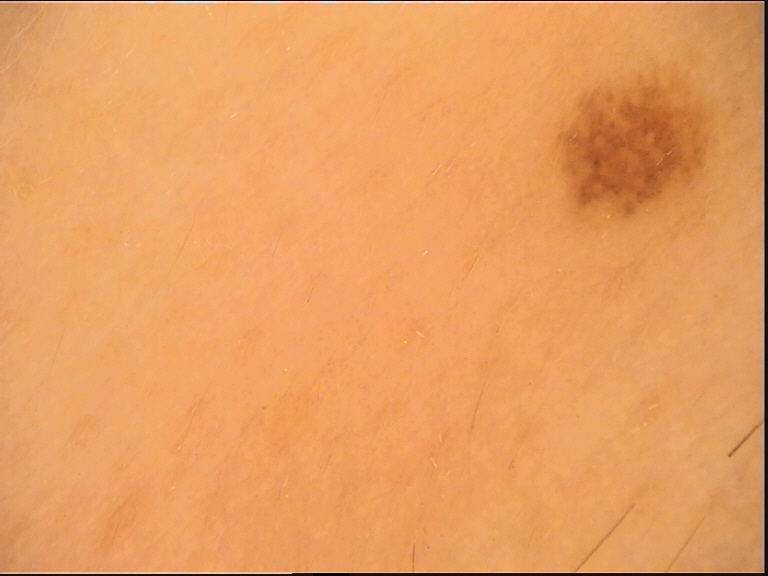Case:
– class · dysplastic junctional nevus (expert consensus)